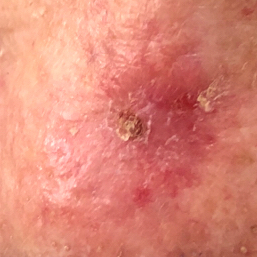patient:
  age: 80
  gender: female
risk_factors:
  positive:
    - prior skin cancer (patient or family)
image: clinical photo
lesion_location: the nose
lesion_size:
  diameter_1_mm: 10.0
  diameter_2_mm: 8.0
symptoms:
  present:
    - bleeding
    - elevation
    - pain
    - itching
diagnosis:
  name: basal cell carcinoma
  code: BCC
  malignancy: malignant
  confirmation: histopathology